A skin lesion imaged with a dermatoscope — 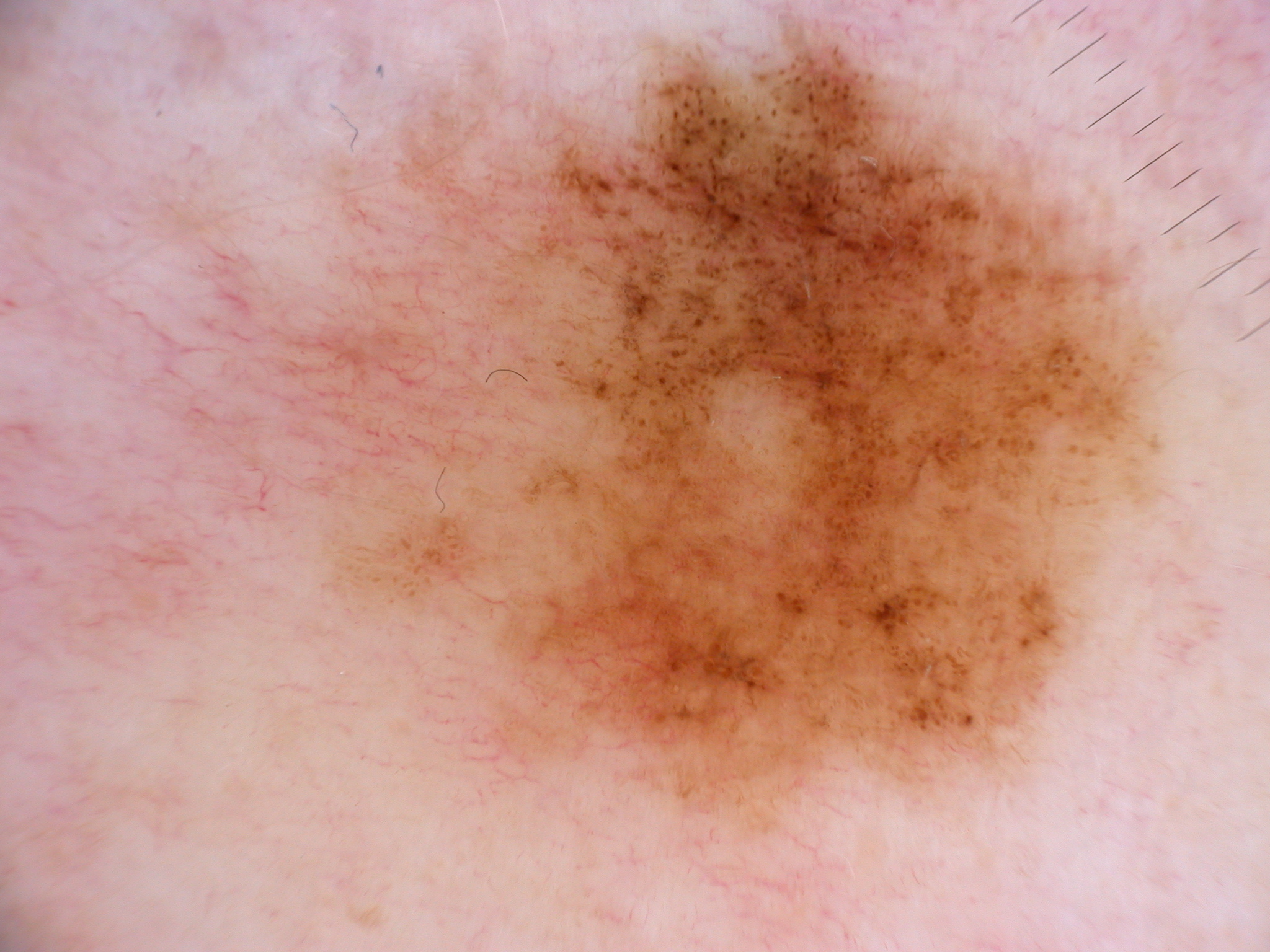Findings: Dermoscopy demonstrates globules and pigment network; no milia-like cysts, streaks, or negative network. The lesion's extent is left=256, top=7, right=1197, bottom=857. A large lesion occupying much of the field. Conclusion: The biopsy diagnosis was a melanoma.